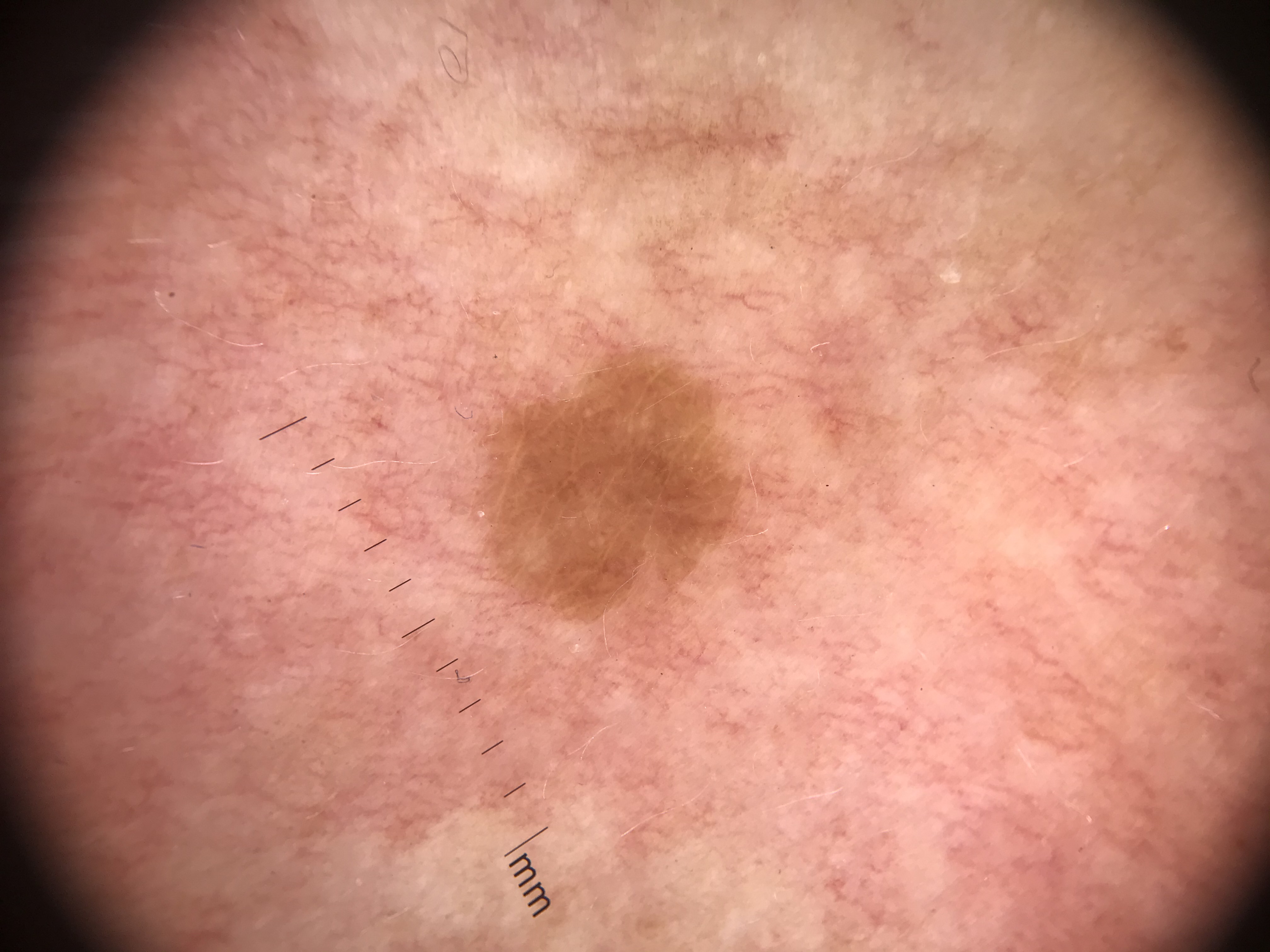modality: dermoscopy
subtype: keratinocytic
assessment: seborrheic keratosis (expert consensus)